Dermoscopy of a skin lesion.
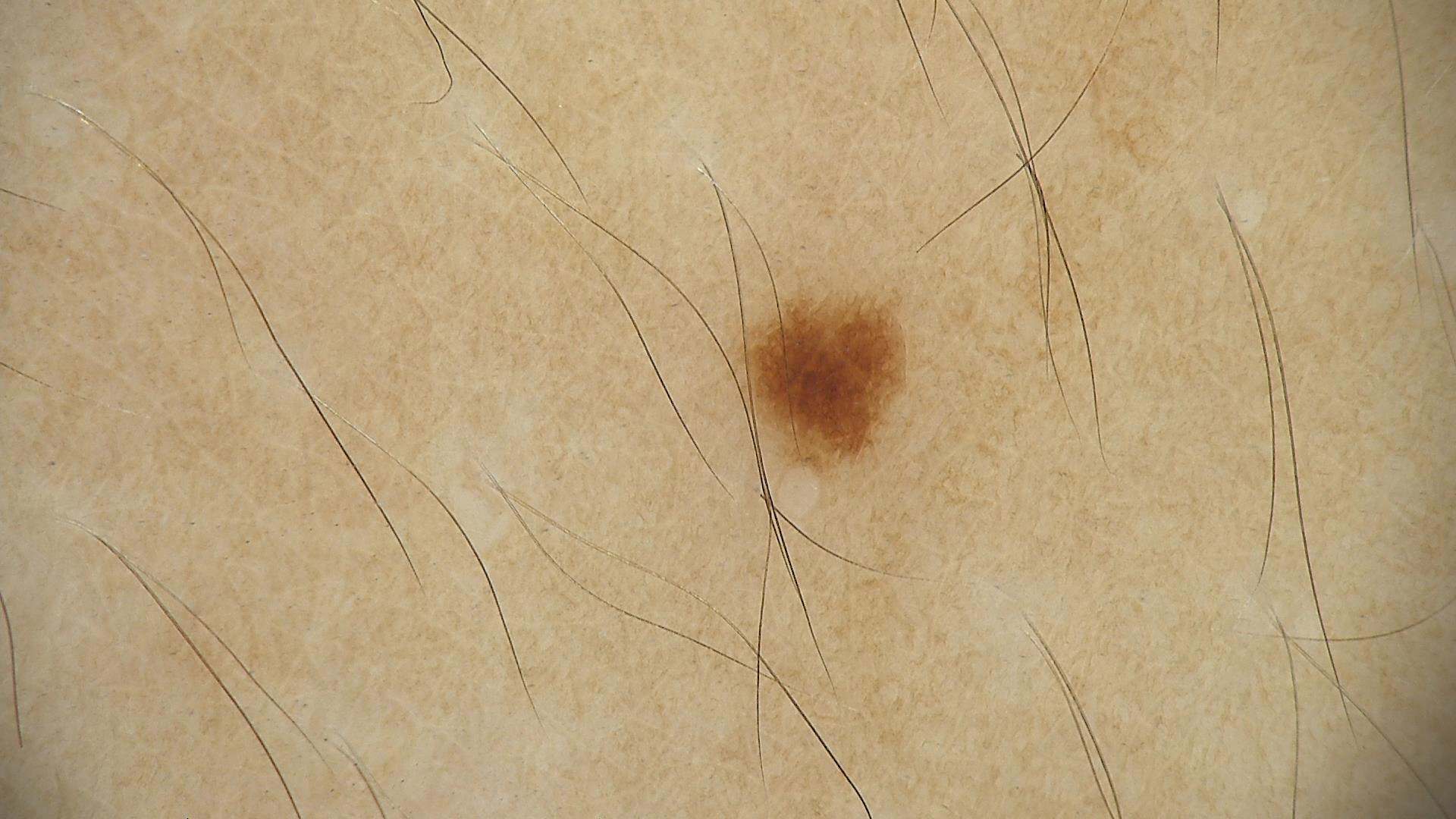assessment: dysplastic junctional nevus (expert consensus).